A clinical close-up photograph of a skin lesion · a subject in their 80s: 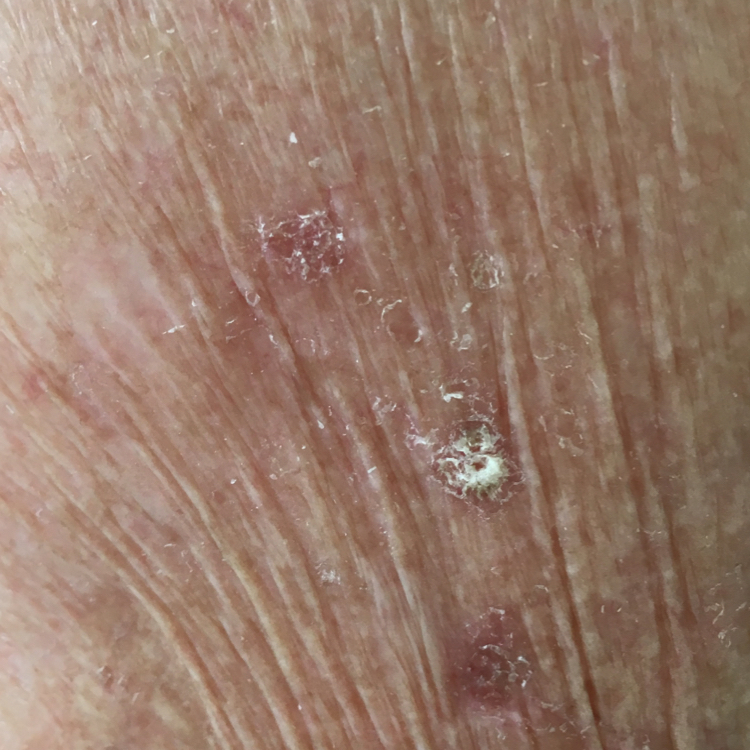  symptoms:
    present:
      - itching
  diagnosis:
    name: actinic keratosis
    code: ACK
    malignancy: indeterminate
    confirmation: clinical consensus